The lesion involves the arm · the photograph is a close-up of the affected area — 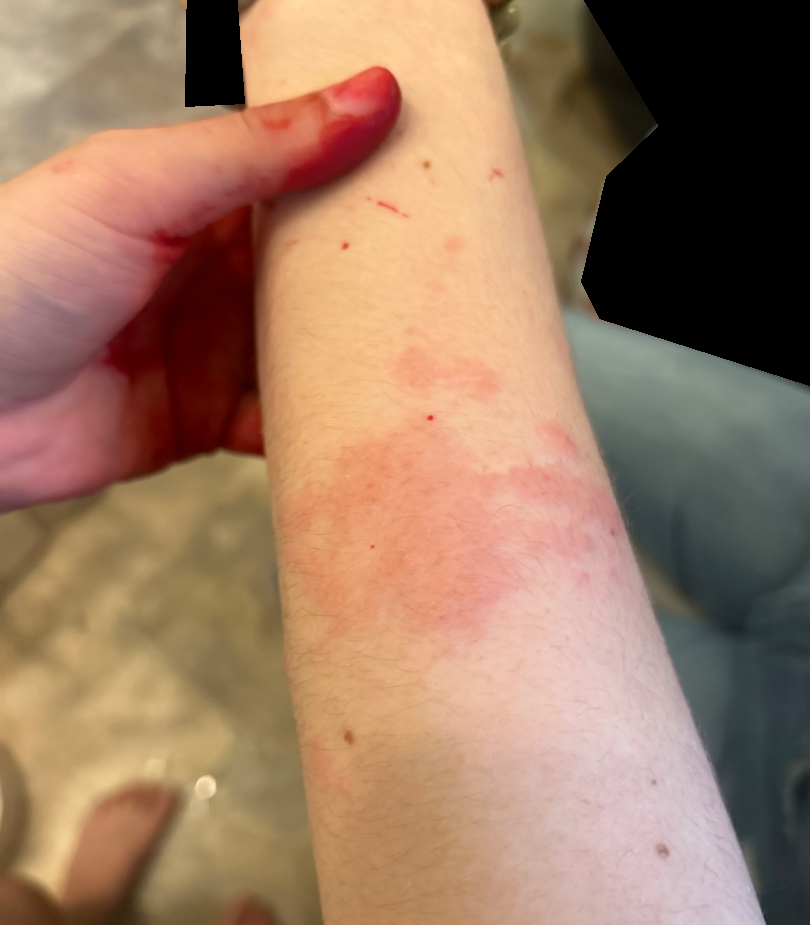| field | value |
|---|---|
| patient describes the issue as | a rash |
| present for | less than one week |
| lesion texture | raised or bumpy and fluid-filled |
| symptoms | itching |
| differential | in keeping with Acute dermatitis, NOS |